The affected area is the back of the torso, head or neck, arm, leg and front of the torso. The subject is 18–29, female. Fitzpatrick II; lay reviewers estimated a Monk skin tone scale of 2. The patient considered this a rash. Reported lesion symptoms include itching. Close-up view.
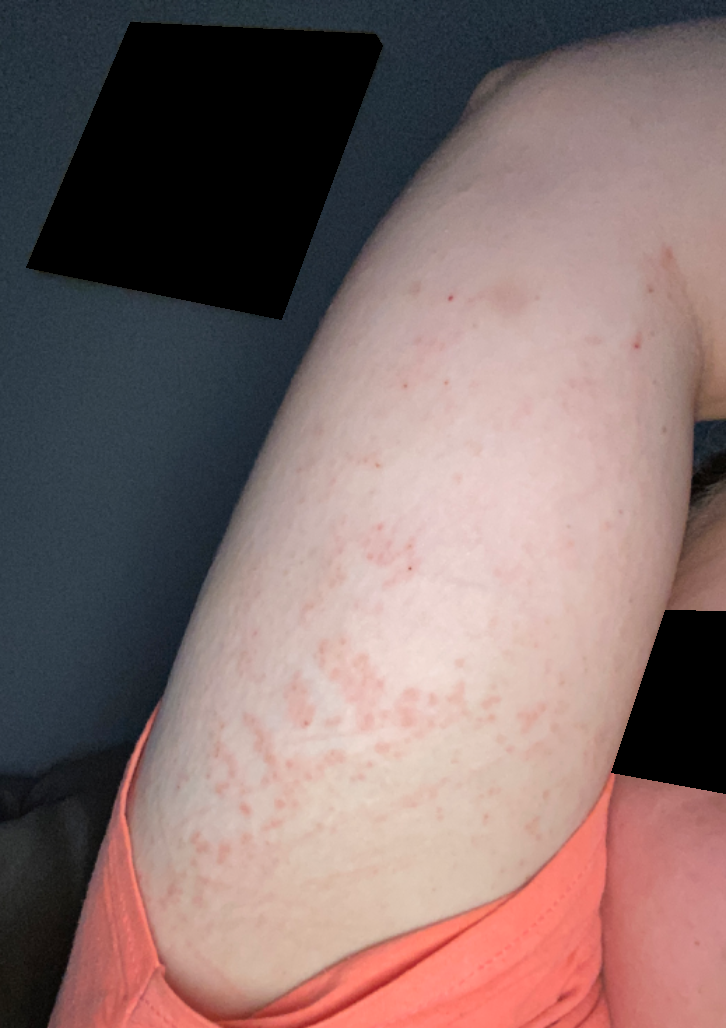<dermatology_case>
<differential>
  <leading>Allergic Contact Dermatitis</leading>
  <considered>Keratosis pilaris, Eczema</considered>
</differential>
</dermatology_case>